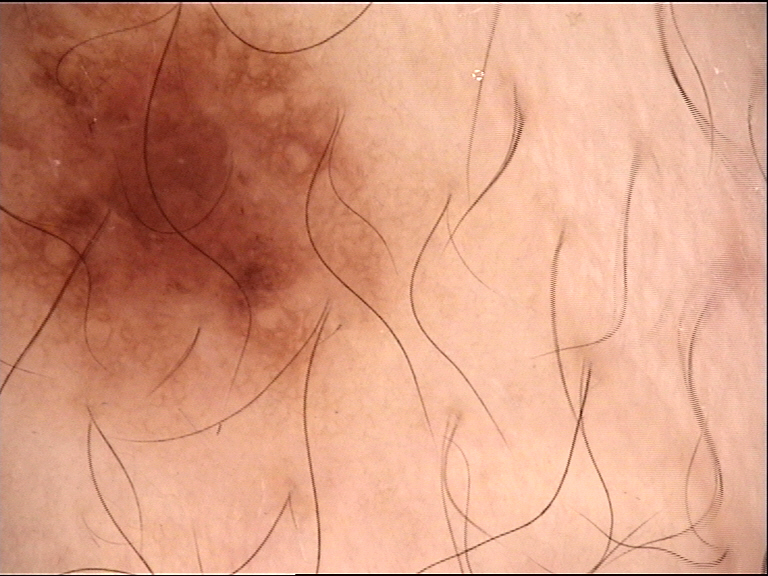| key | value |
|---|---|
| diagnostic label | dysplastic junctional nevus (expert consensus) |